A dermoscopic photograph of a skin lesion.
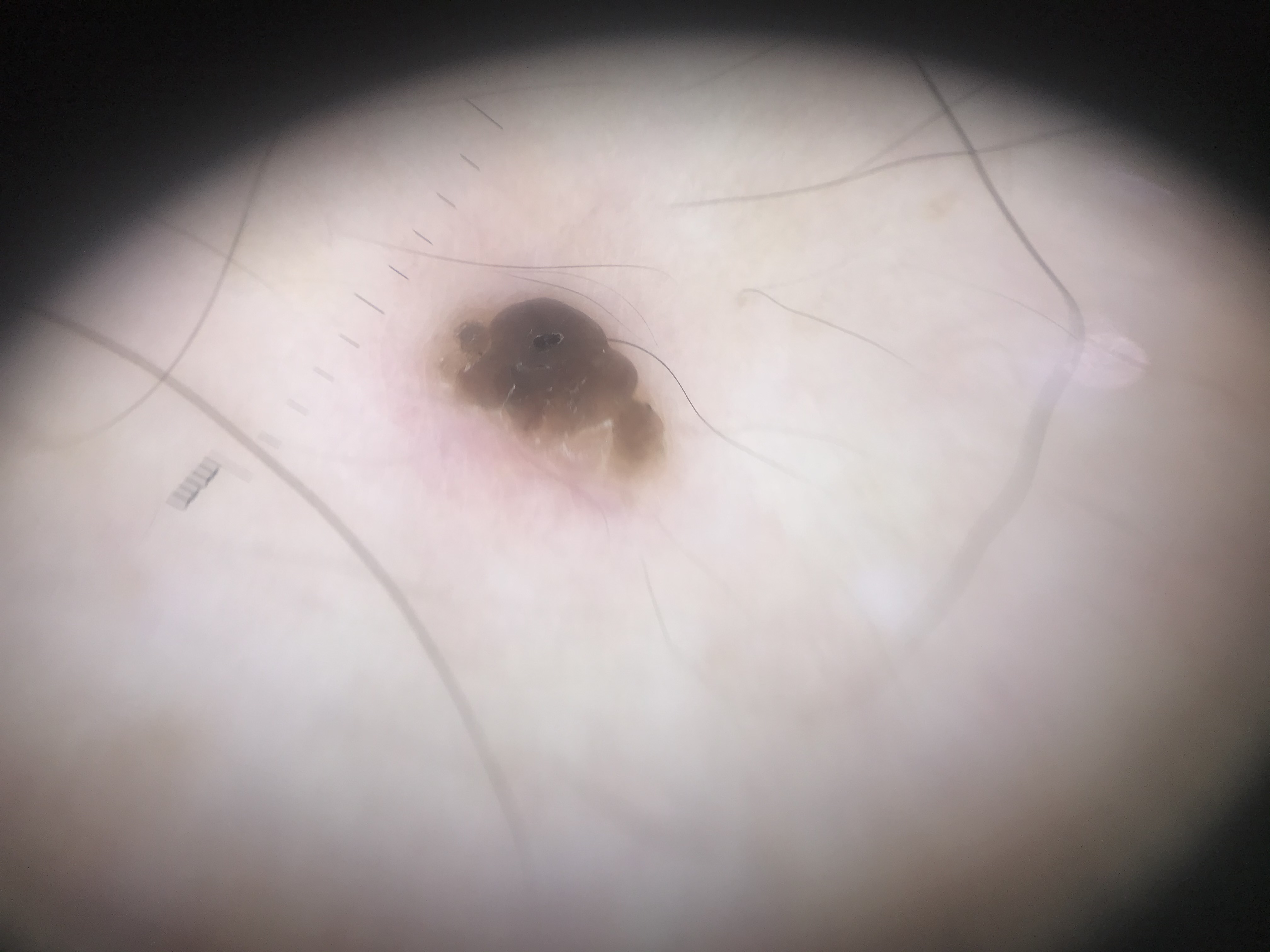Summary:
The morphology is that of a keratinocytic lesion.
Impression:
The diagnostic label was a seborrheic keratosis.